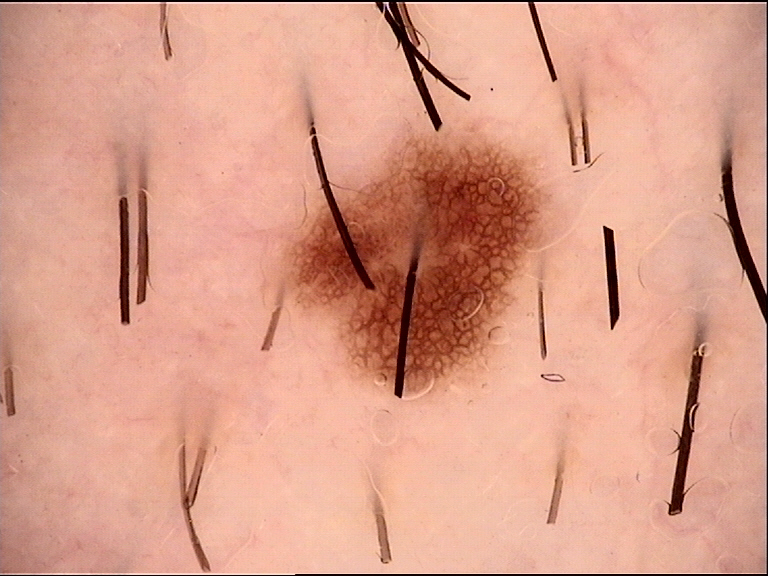The diagnosis was a dysplastic junctional nevus.